Dermoscopy of a skin lesion; a female patient aged 63 to 67:
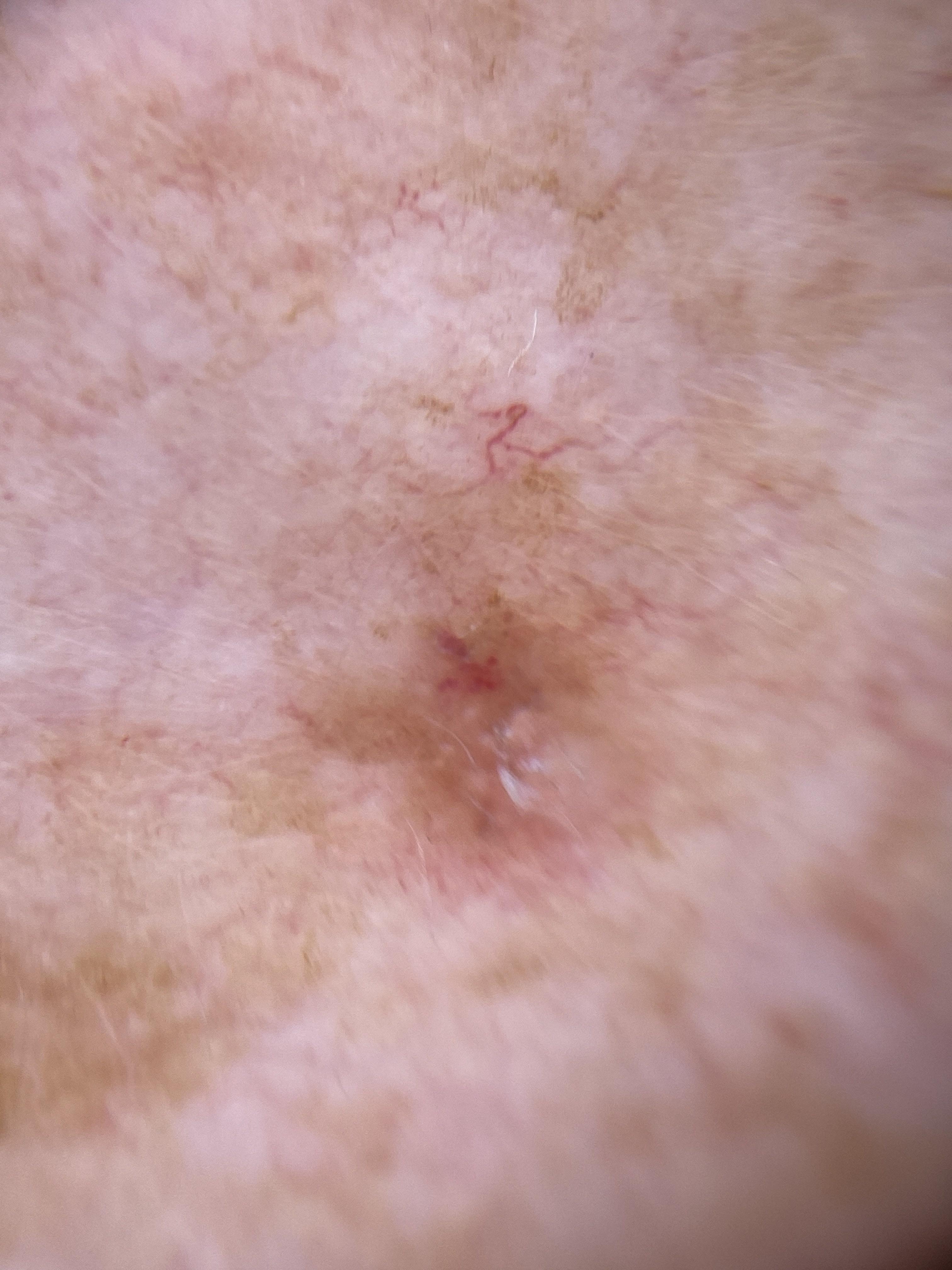{"lesion_location": {"region": "the trunk", "detail": "the anterior trunk"}, "diagnosis": {"name": "Squamous cell carcinoma", "malignancy": "malignant", "confirmation": "histopathology", "lineage": "epidermal"}}